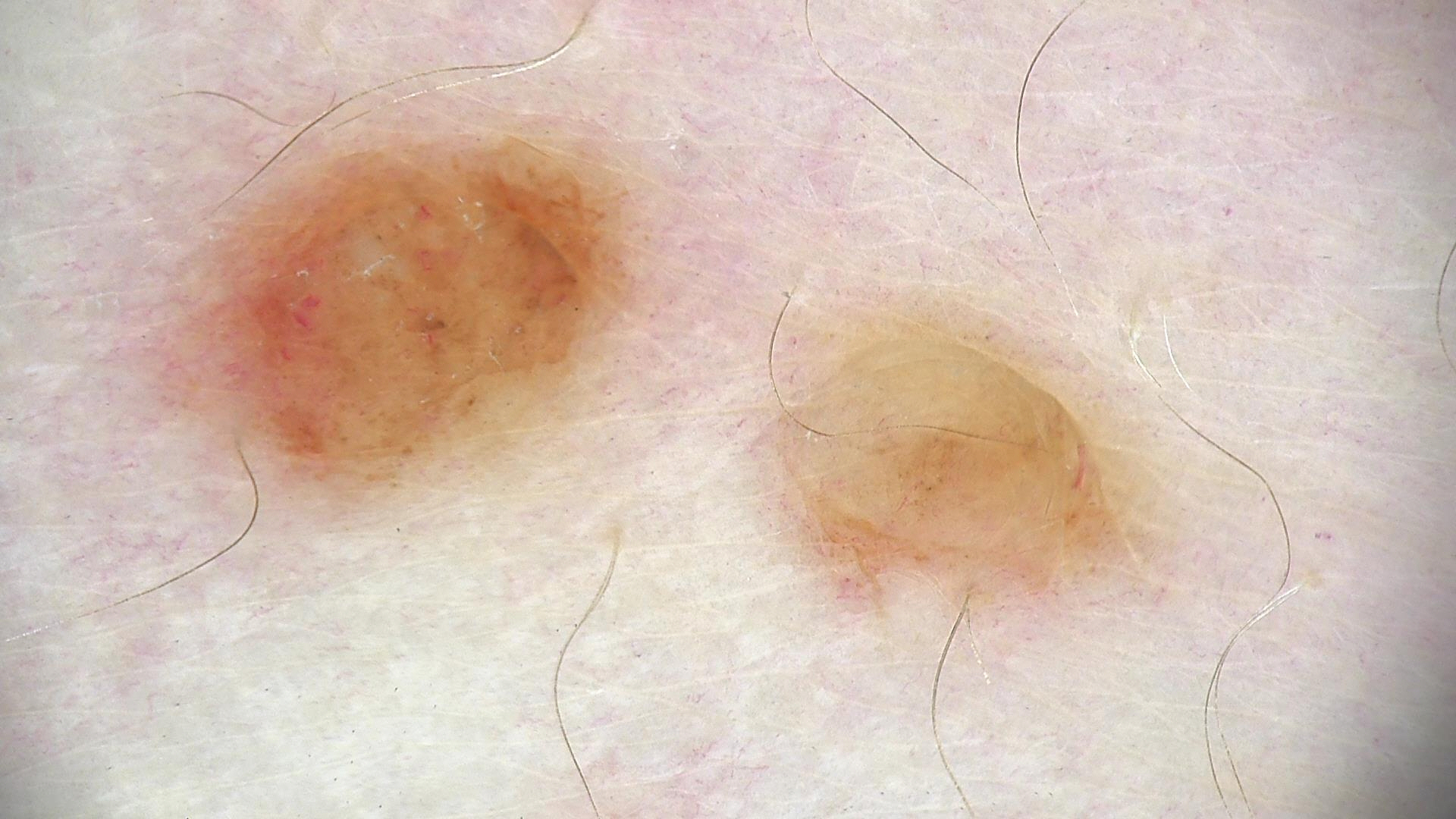Conclusion:
The diagnostic label was a dermal nevus.